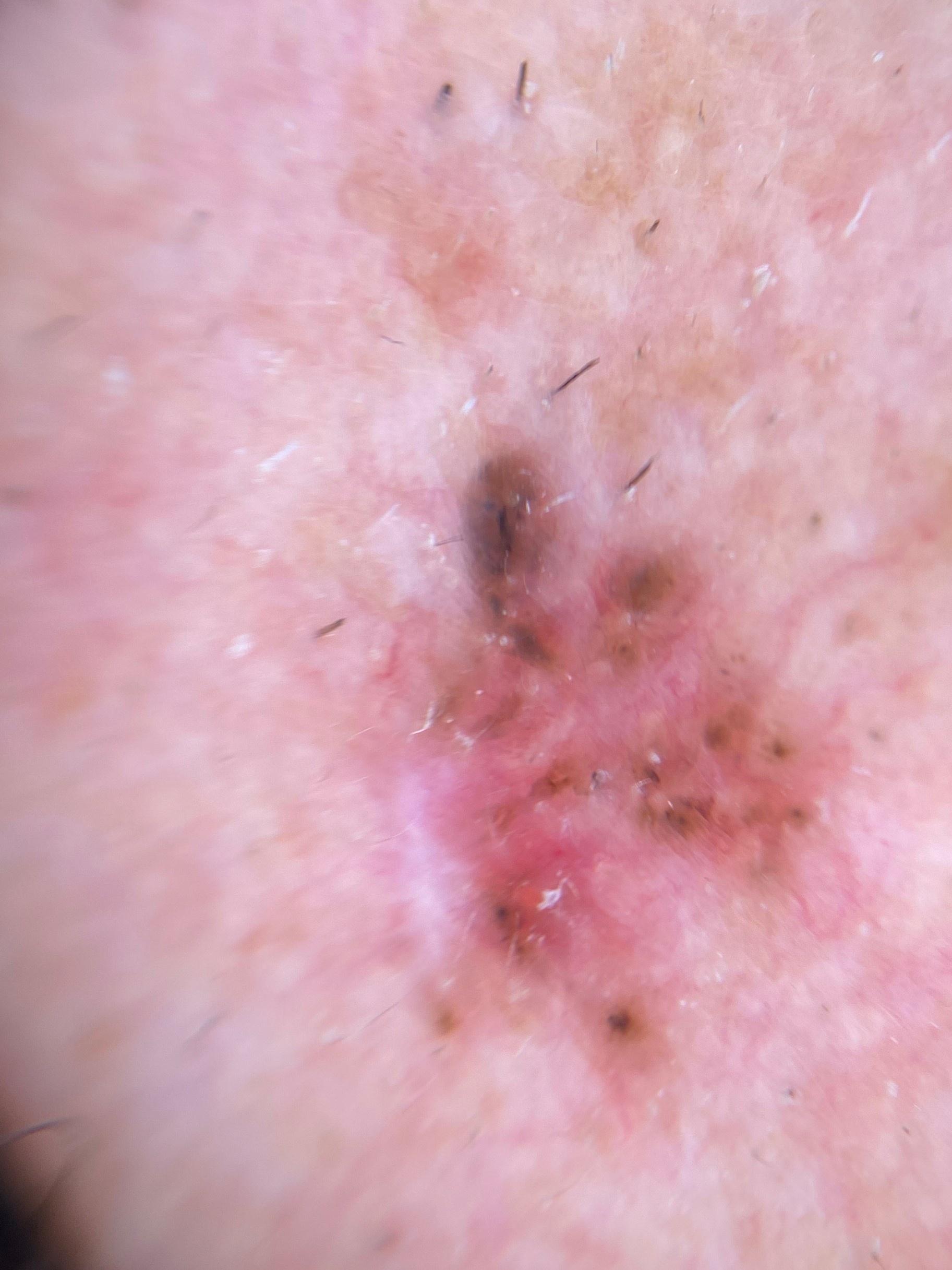{
  "image": "dermoscopy",
  "patient": {
    "age_approx": 75,
    "sex": "male"
  },
  "lesion_location": {
    "region": "the head or neck"
  },
  "diagnosis": {
    "name": "Basal cell carcinoma",
    "malignancy": "malignant",
    "confirmation": "histopathology",
    "lineage": "adnexal"
  }
}